The palm is involved, the photo was captured at a distance — 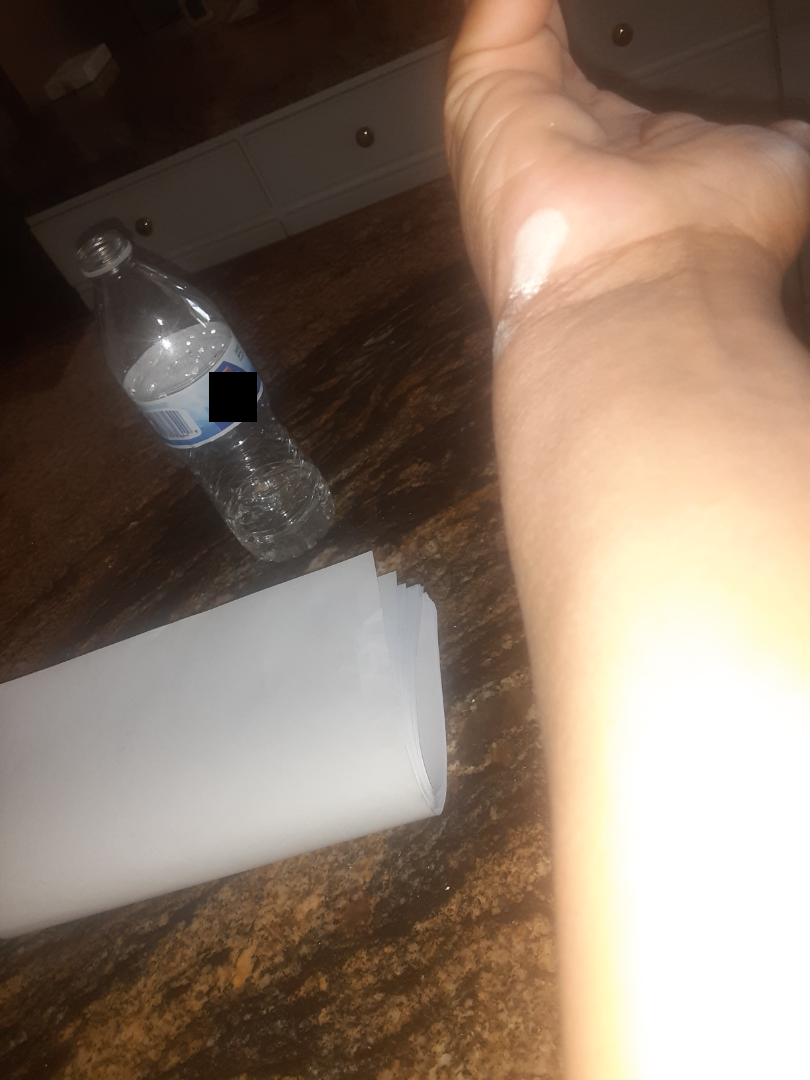| feature | finding |
|---|---|
| assessment | could not be assessed |